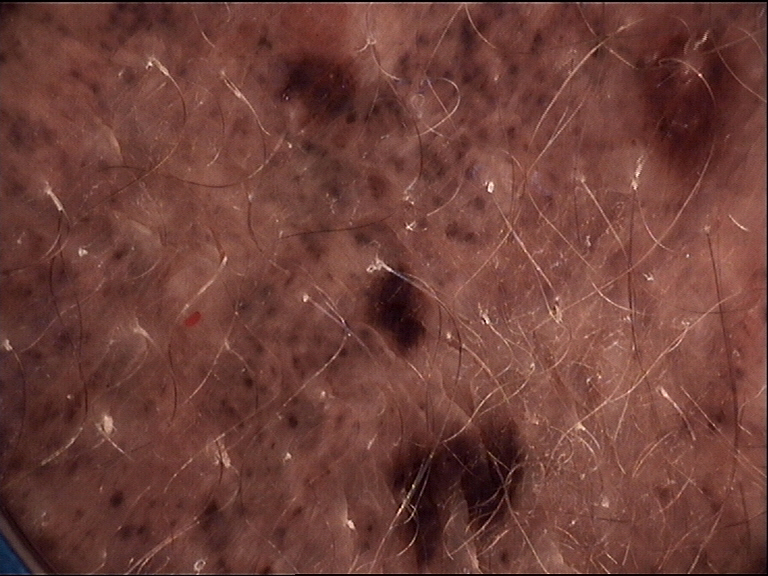Q: What is the imaging modality?
A: dermoscopy
Q: How is the lesion classified?
A: banal
Q: What was the diagnostic impression?
A: congenital compound nevus (expert consensus)